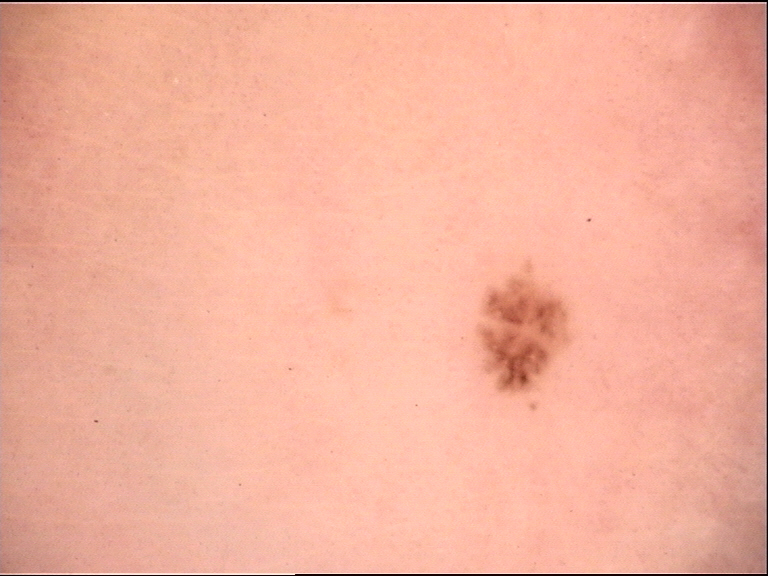A dermatoscopic image of a skin lesion.
The diagnosis was a banal lesion — a junctional nevus.